A dermoscopy image of a single skin lesion: 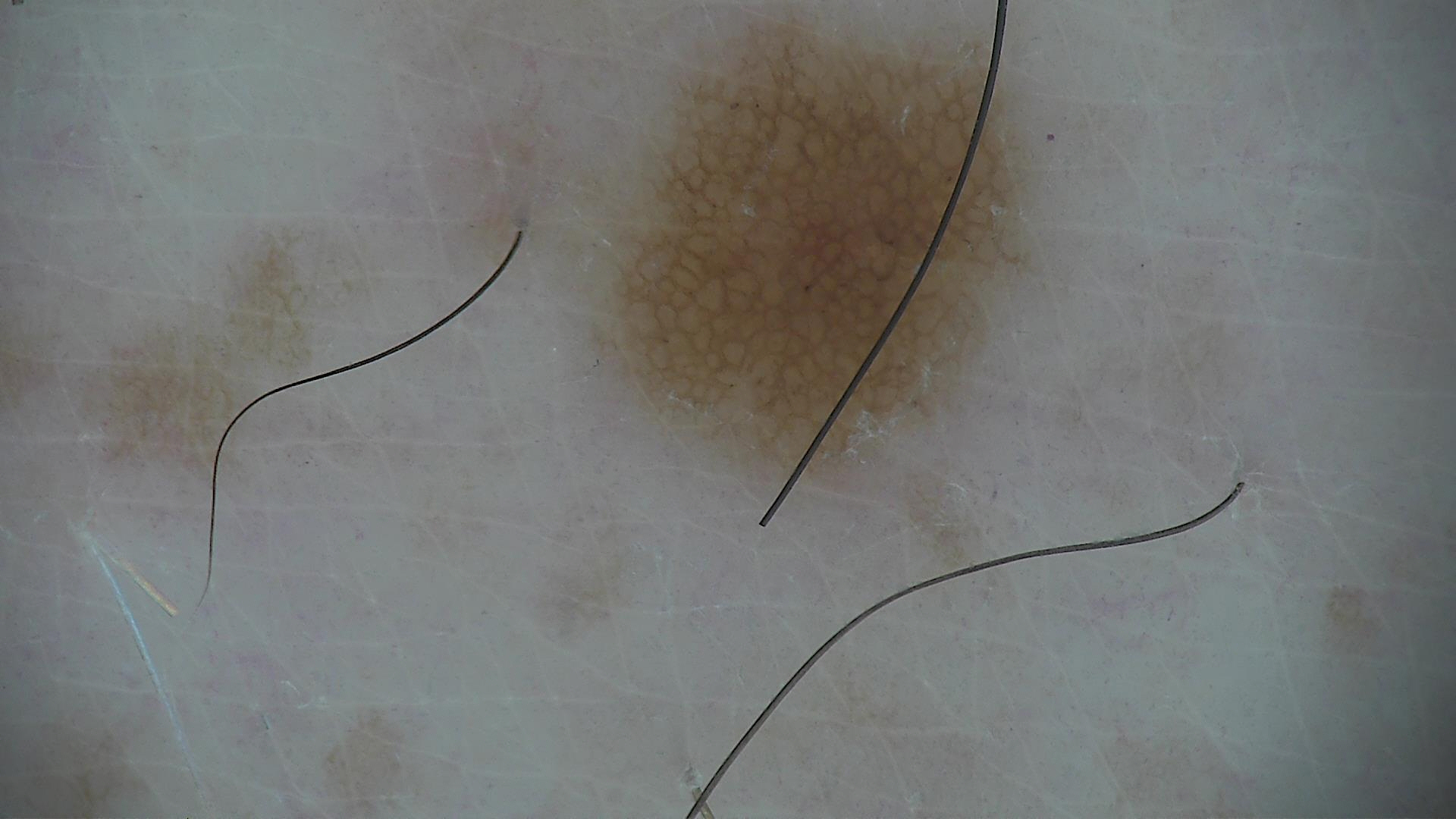Consistent with a benign lesion — a dysplastic junctional nevus.